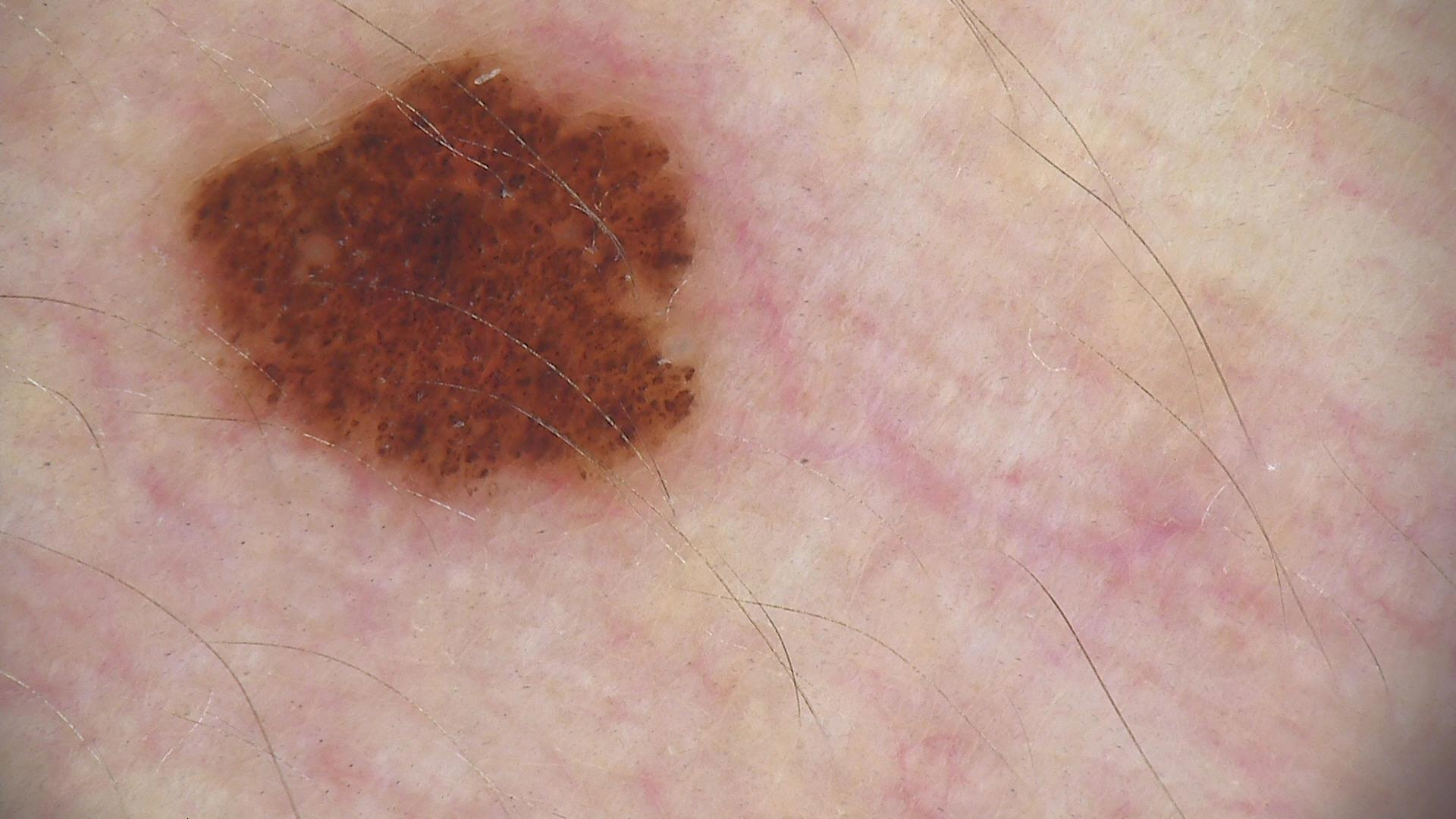Findings:
A dermatoscopic image of a skin lesion.
Impression:
The diagnosis was a benign lesion — a dysplastic junctional nevus.